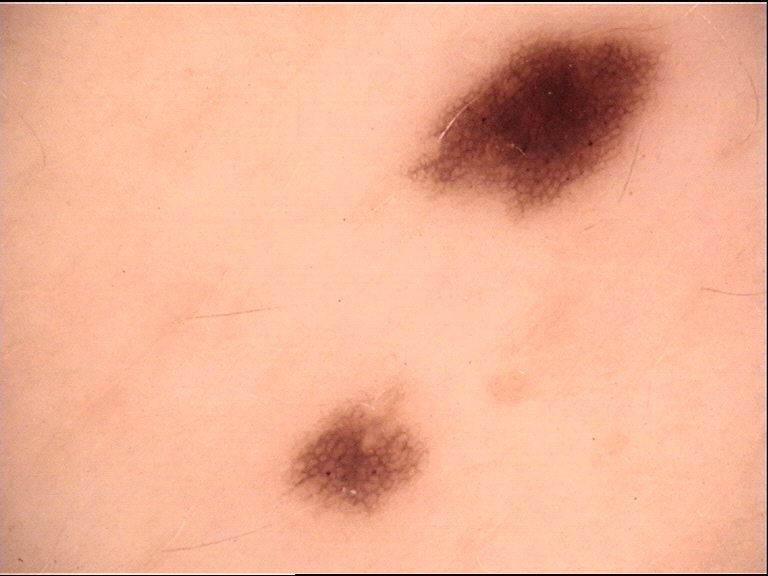<case>
  <diagnosis>
    <name>dysplastic junctional nevus</name>
    <code>jd</code>
    <malignancy>benign</malignancy>
    <super_class>melanocytic</super_class>
    <confirmation>expert consensus</confirmation>
  </diagnosis>
</case>